Texture is reported as raised or bumpy · the condition has been present for about one day · the contributor is 18–29, female · the top or side of the foot is involved · an image taken at a distance · no relevant systemic symptoms · reported lesion symptoms include bothersome appearance and itching · skin tone: FST II; lay reviewers estimated MST 2–3: 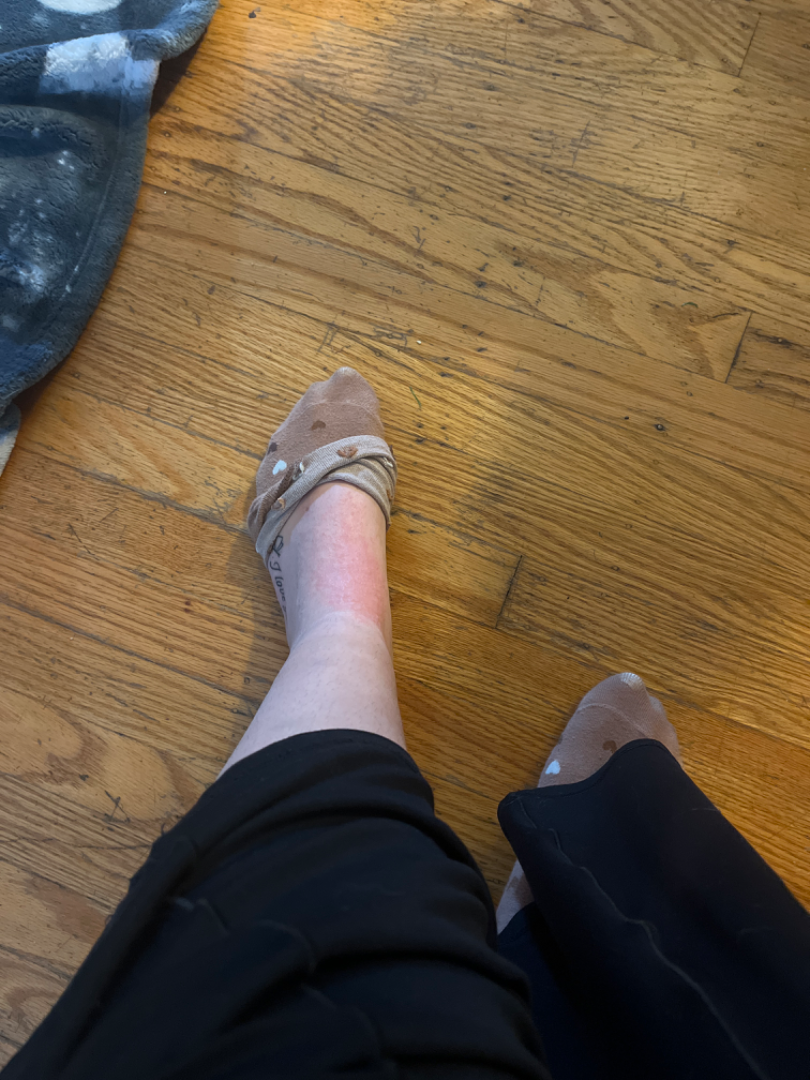diagnostic considerations = most likely Allergic Contact Dermatitis.